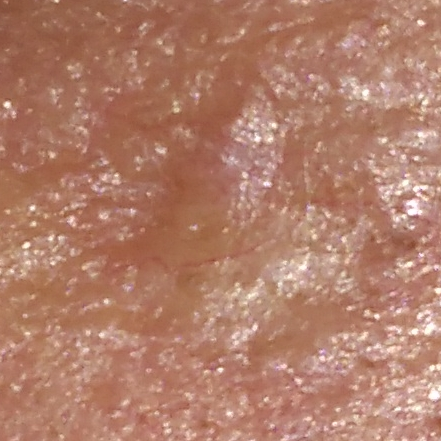The biopsy diagnosis was a basal cell carcinoma.